This is a dermoscopic photograph of a skin lesion:
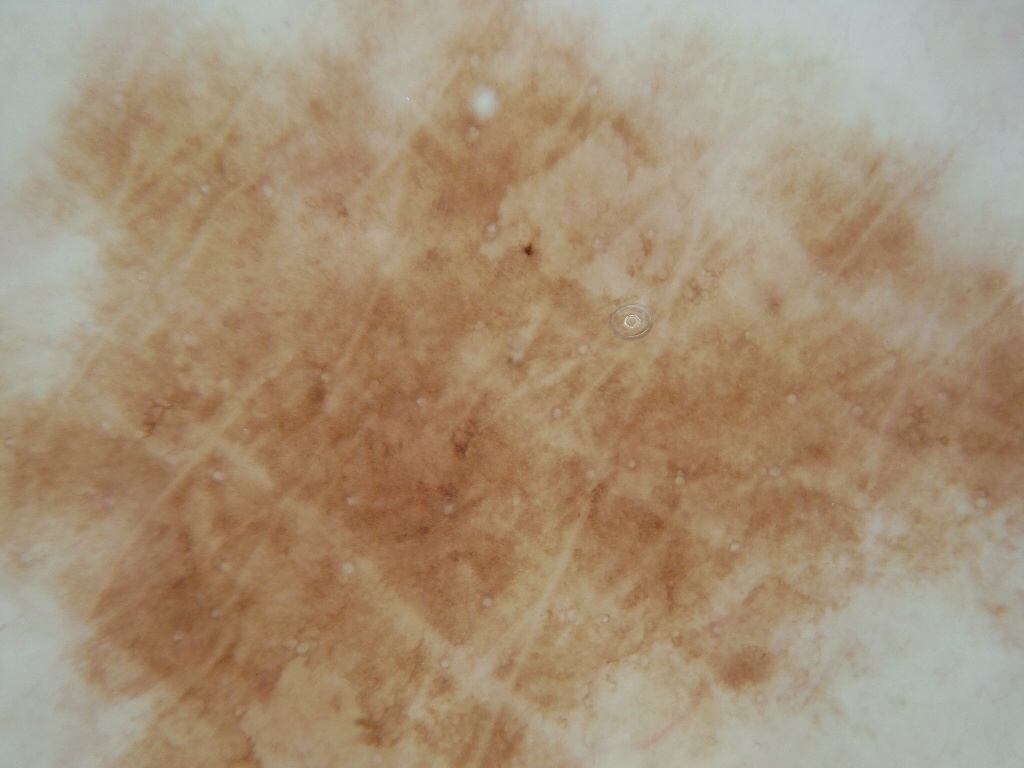Summary: The lesion reaches across nearly the entire image. Impression: Consistent with a melanocytic nevus, a benign lesion.